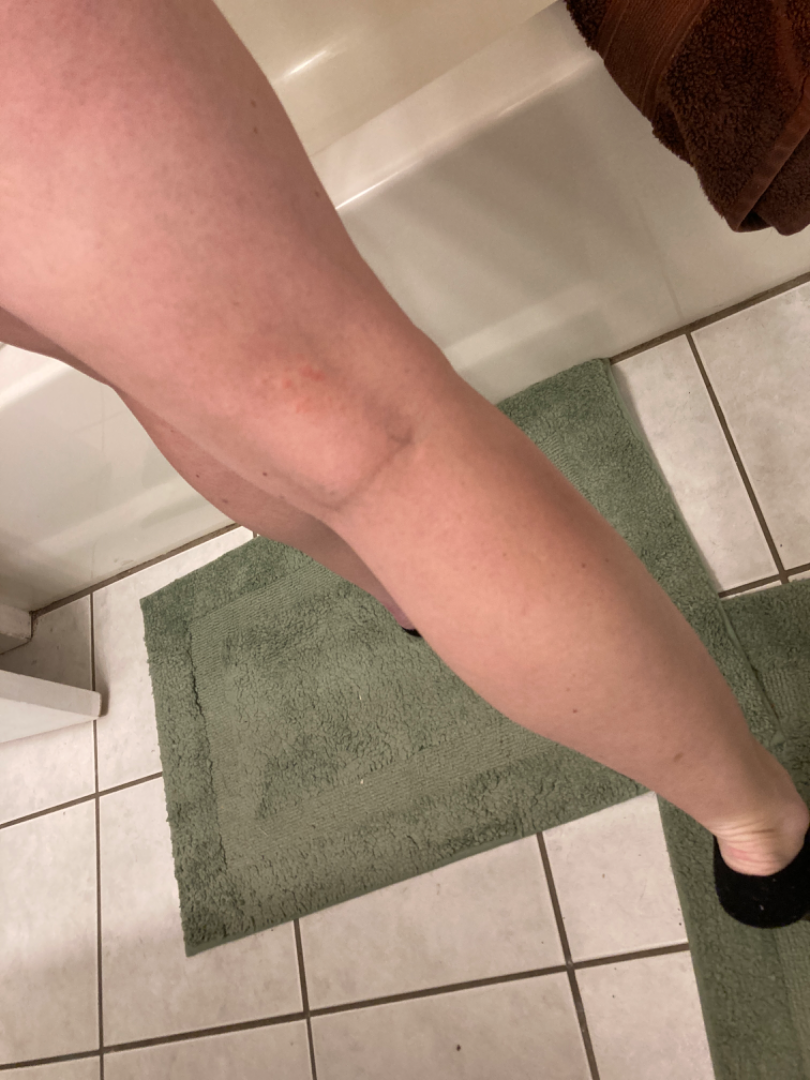This image was taken at a distance. The subject is 30–39, female. The leg is involved. The lesion is described as raised or bumpy. The patient reports the condition has been present for about one day. The lesion is associated with itching. The leading consideration is Hypersensitivity; also consider Eczema.